Imaged for a research study, with no referral diagnosis recorded; a male subject 83 years of age; the patient says their skin reddens with sun exposure; a dermoscopic image of a skin lesion:
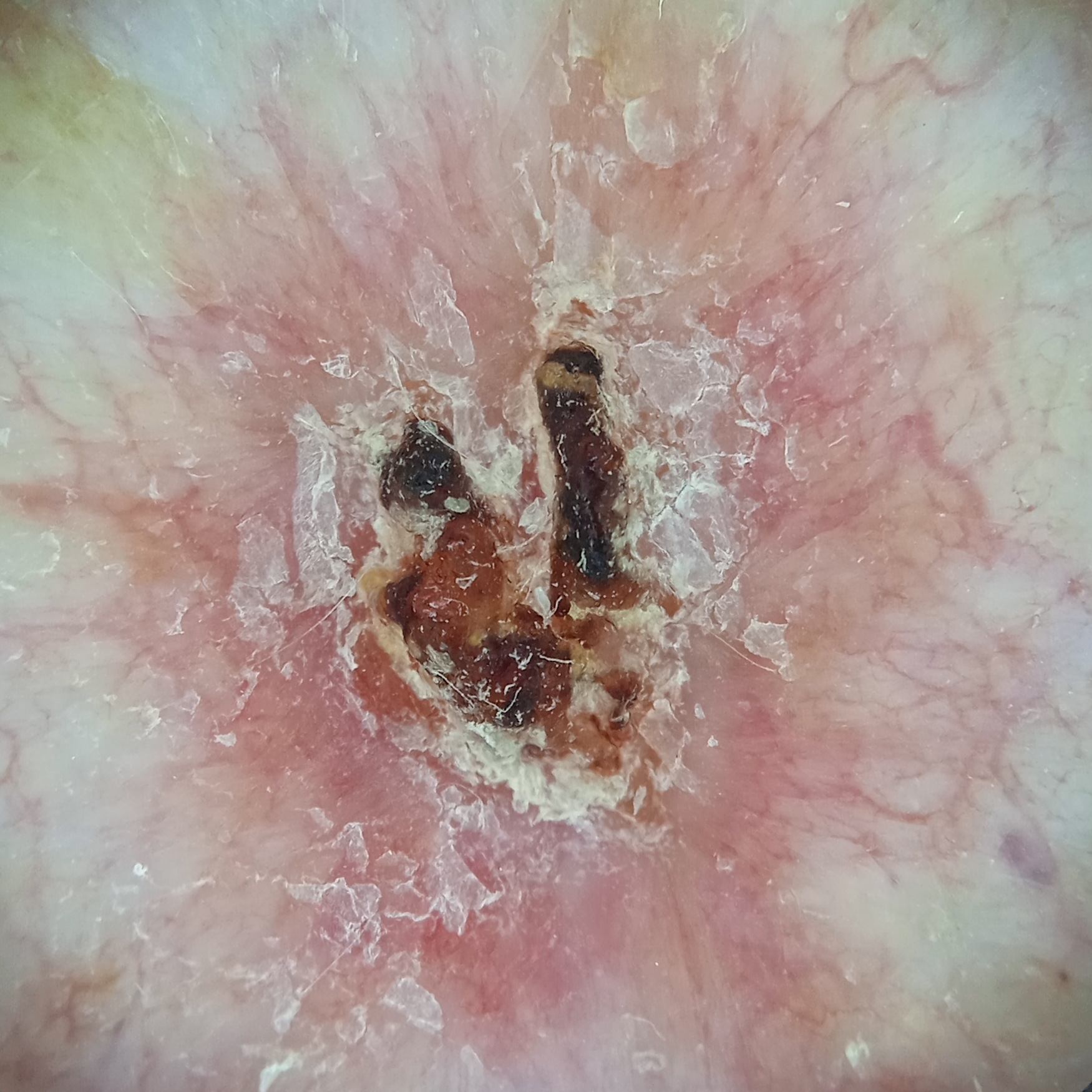Clinical context: The lesion is located on the back. Conclusion: The dermatologists' assessment was a basal cell carcinoma.